Imaged for a research study, with no referral diagnosis recorded. A female patient 26 years old. A dermatoscopic image of a skin lesion — 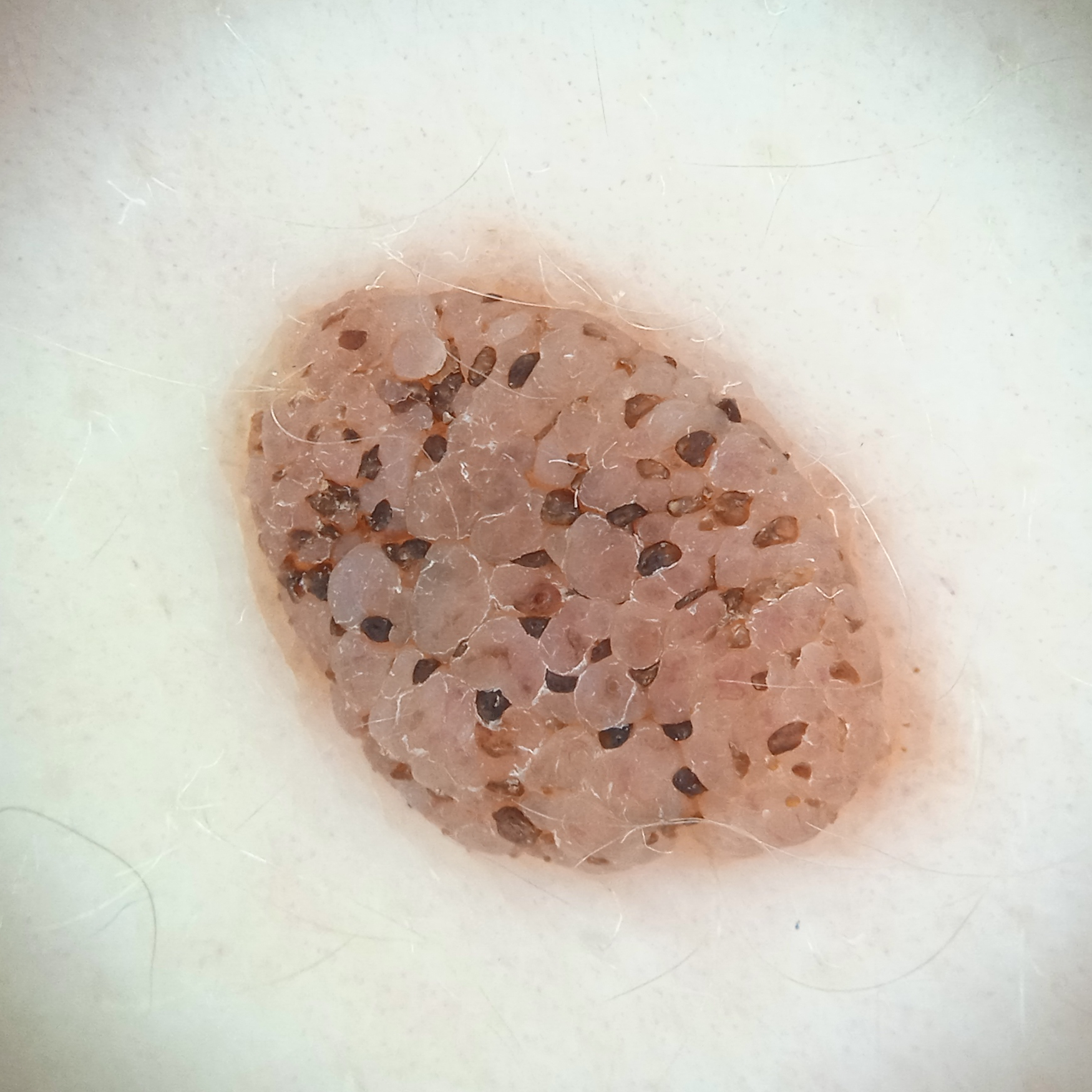Case:
- assessment — seborrheic keratosis (dermatologist consensus)